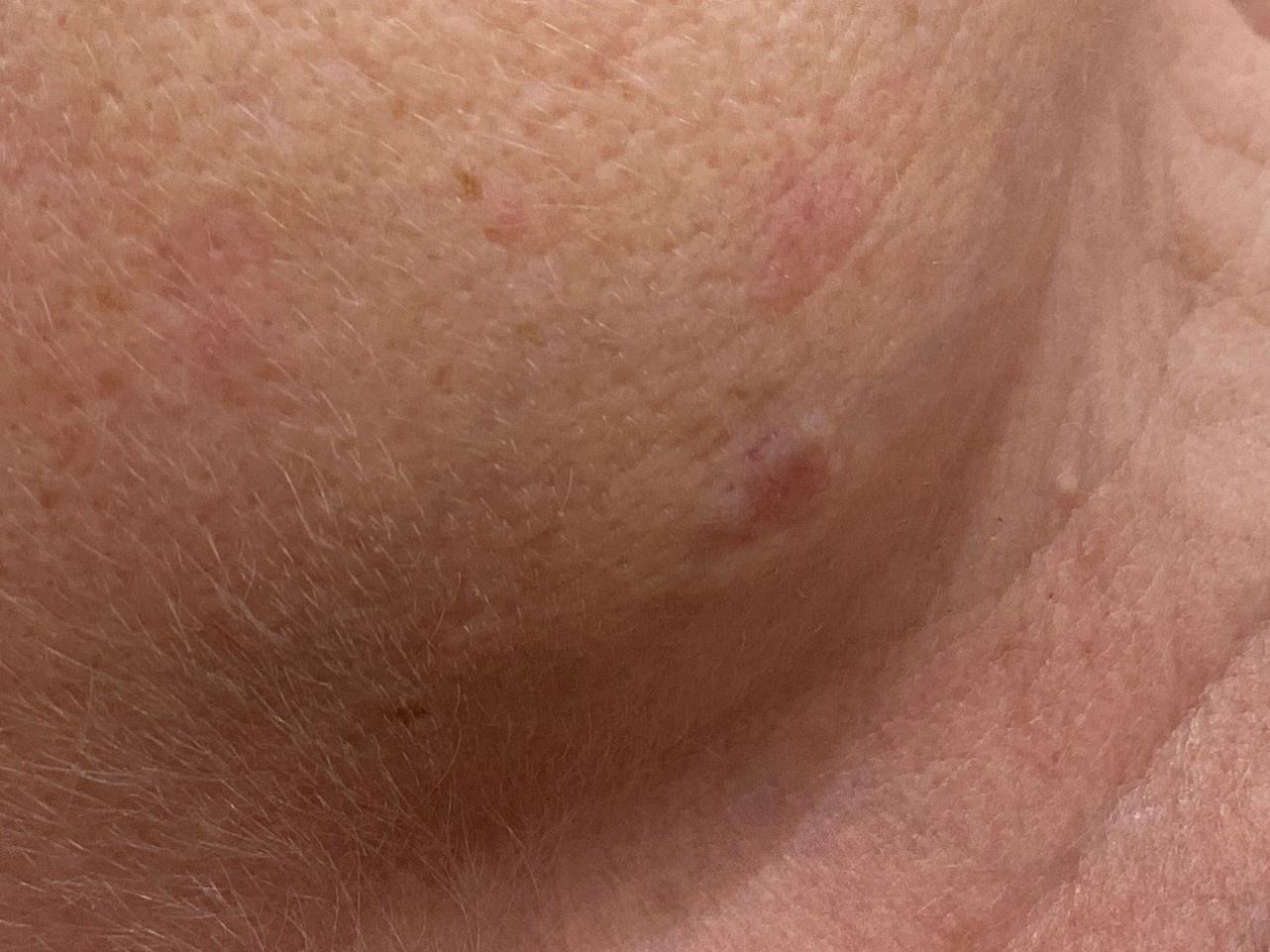Q: How was this image acquired?
A: clinical photograph
Q: Who is the patient?
A: female, in their mid- to late 70s
Q: Where on the body is the lesion?
A: the head or neck
Q: What did the workup show?
A: Basal cell carcinoma (biopsy-proven)